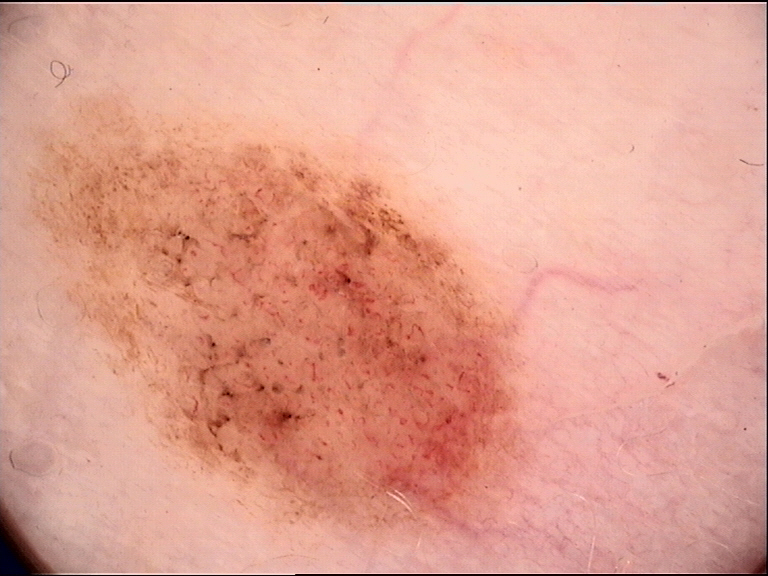A dermoscopy image of a single skin lesion. Classified as a banal lesion — a compound nevus.